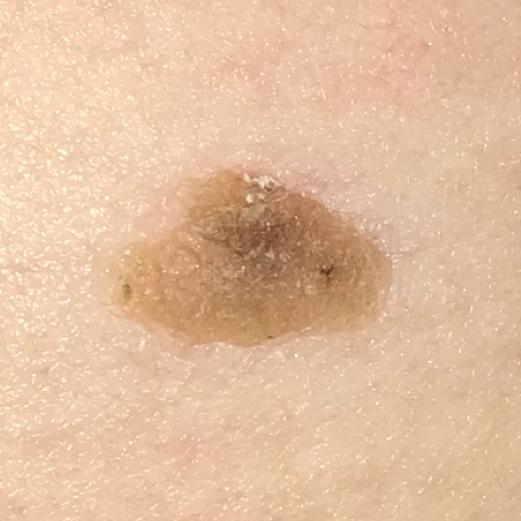A clinical photograph showing a skin lesion. A subject in their 50s. The lesion was found on the abdomen. The patient describes that the lesion is elevated and has grown. Consistent with a seborrheic keratosis.